A dermoscopic close-up of a skin lesion:
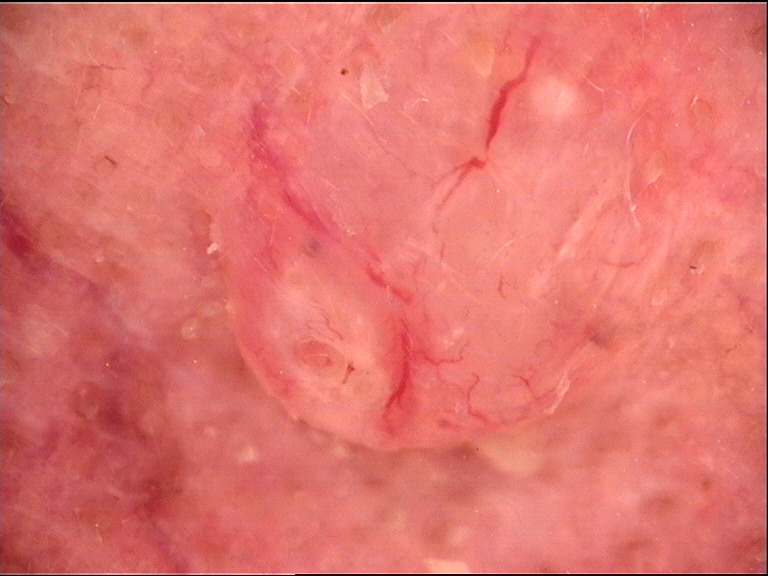class: basal cell carcinoma (biopsy-proven)